The photo was captured at a distance · the contributor is 50–59, female: 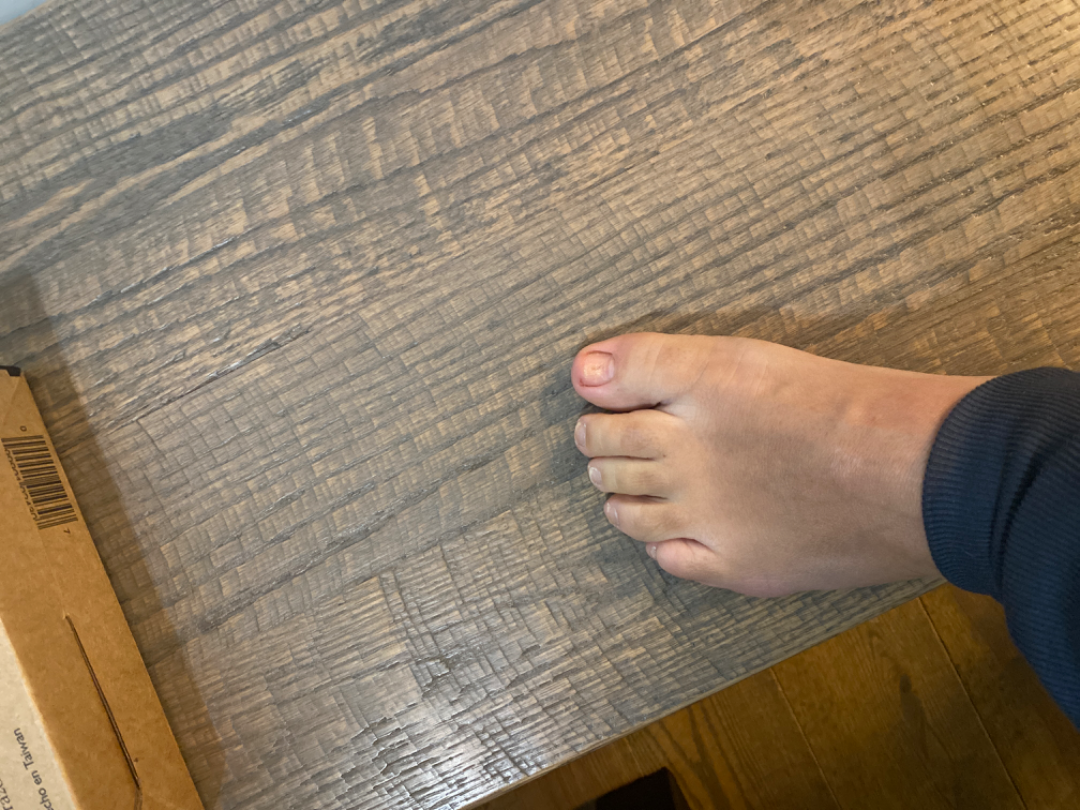Patient information: Reported duration is one to three months. Skin tone: FST III. The contributor reports bothersome appearance. The contributor reports the lesion is raised or bumpy. Self-categorized by the patient as a nail problem. Review: On dermatologist assessment of the image: the favored diagnosis is Onychodystrophy; with consideration of Onychomycosis.